This is a dermoscopic photograph of a skin lesion; a female patient, aged 18 to 22.
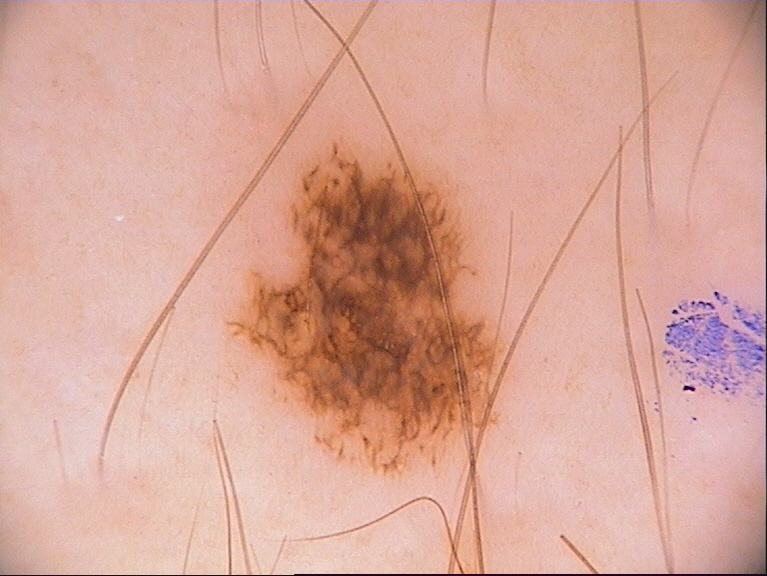  dermoscopic_features:
    present:
      - pigment network
    absent:
      - globules
      - milia-like cysts
      - streaks
      - negative network
  lesion_location:
    bbox_xyxy:
      - 220
      - 143
      - 517
      - 481
  diagnosis:
    name: melanocytic nevus
    malignancy: benign
    lineage: melanocytic
    provenance: clinical